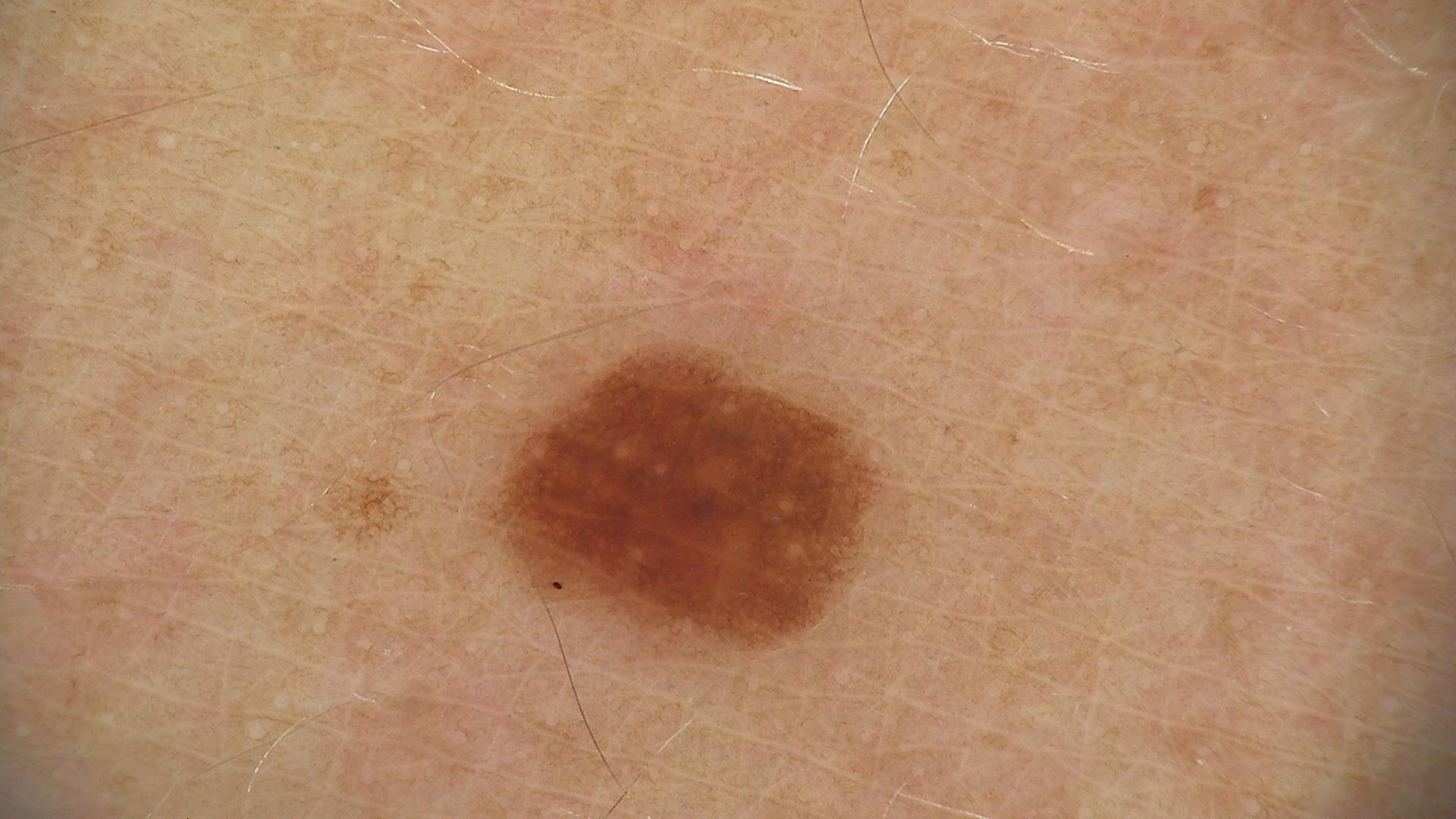– label — dysplastic junctional nevus (expert consensus)